A female patient aged 13-17. A skin lesion imaged with a dermatoscope — 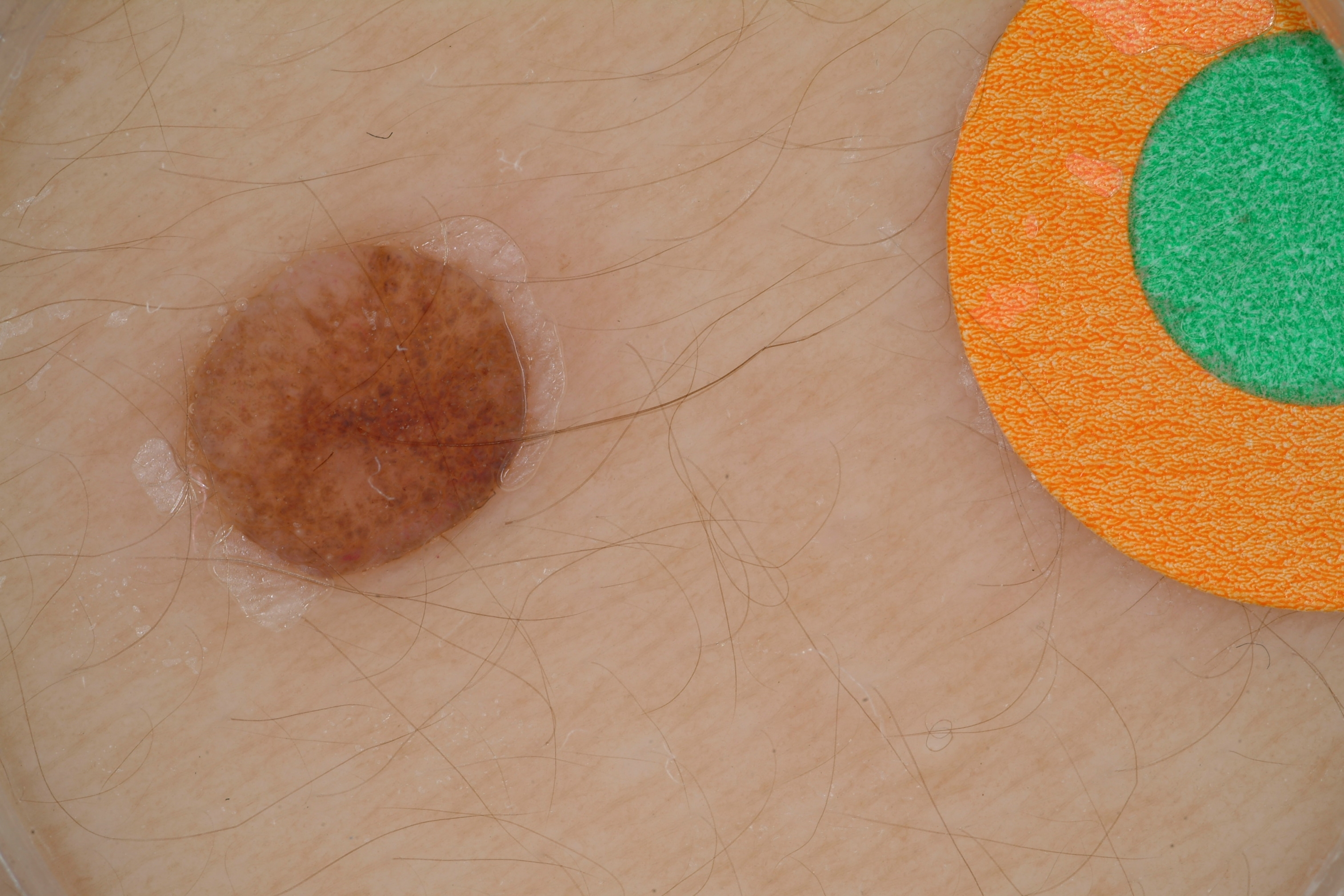<record>
<dermoscopic_features>
  <present>milia-like cysts</present>
  <absent>globules, streaks, pigment network, negative network</absent>
</dermoscopic_features>
<lesion_extent>
  <approx_field_fraction_pct>7</approx_field_fraction_pct>
</lesion_extent>
<lesion_location>
  <bbox_xyxy>181, 239, 533, 580</bbox_xyxy>
</lesion_location>
<diagnosis>
  <name>melanocytic nevus</name>
  <malignancy>benign</malignancy>
  <lineage>melanocytic</lineage>
  <provenance>clinical</provenance>
</diagnosis>
</record>